The patient is a male roughly 55 years of age. This is a dermoscopic photograph of a skin lesion.
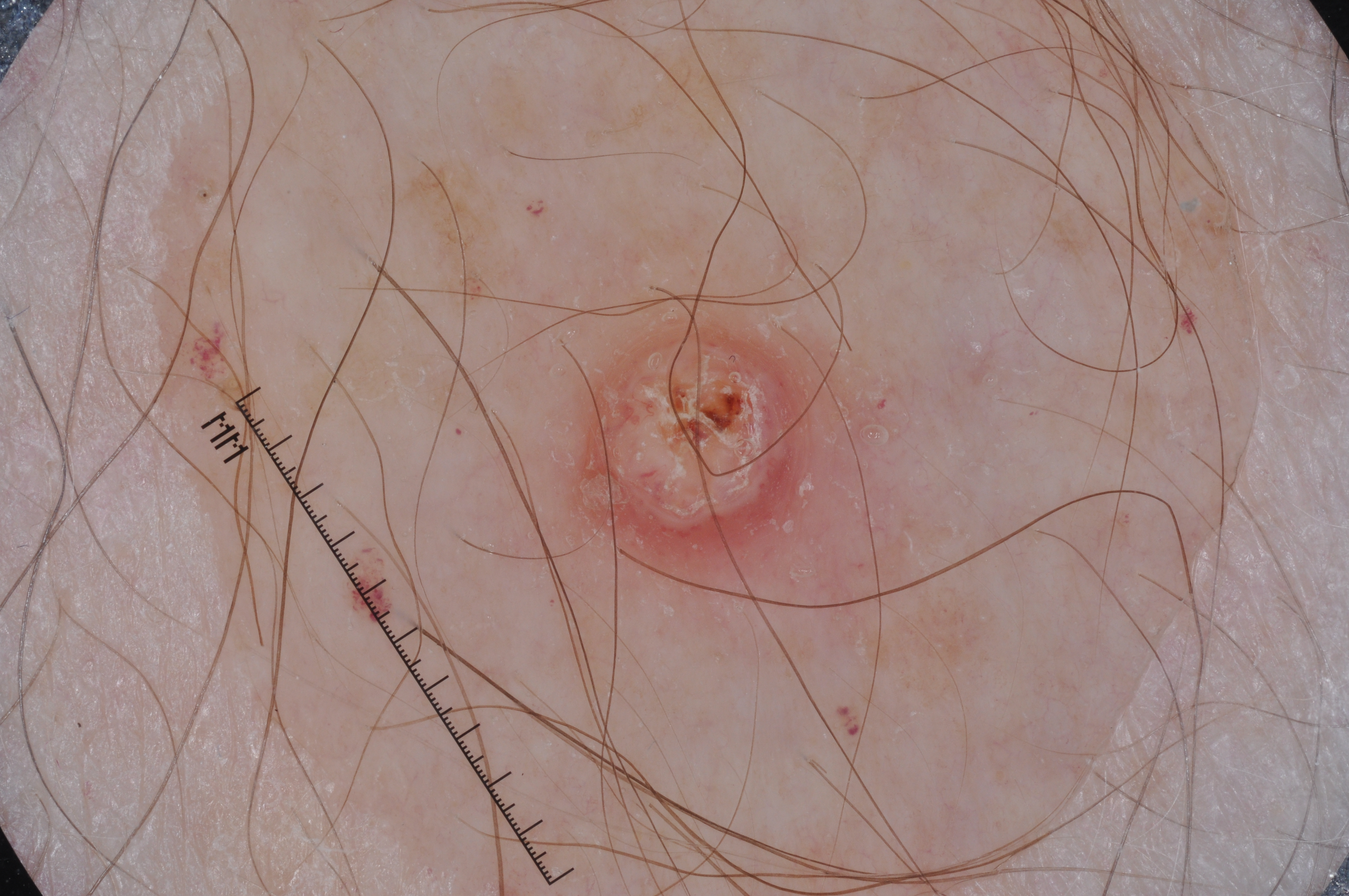Image and clinical context: The lesion spans x1=571 y1=322 x2=832 y2=566. A small lesion occupying a minor part of the field. Dermoscopy demonstrates no streaks, negative network, milia-like cysts, or pigment network. Conclusion: Consistent with a seborrheic keratosis, a benign lesion.